A male subject approximately 40 years of age — 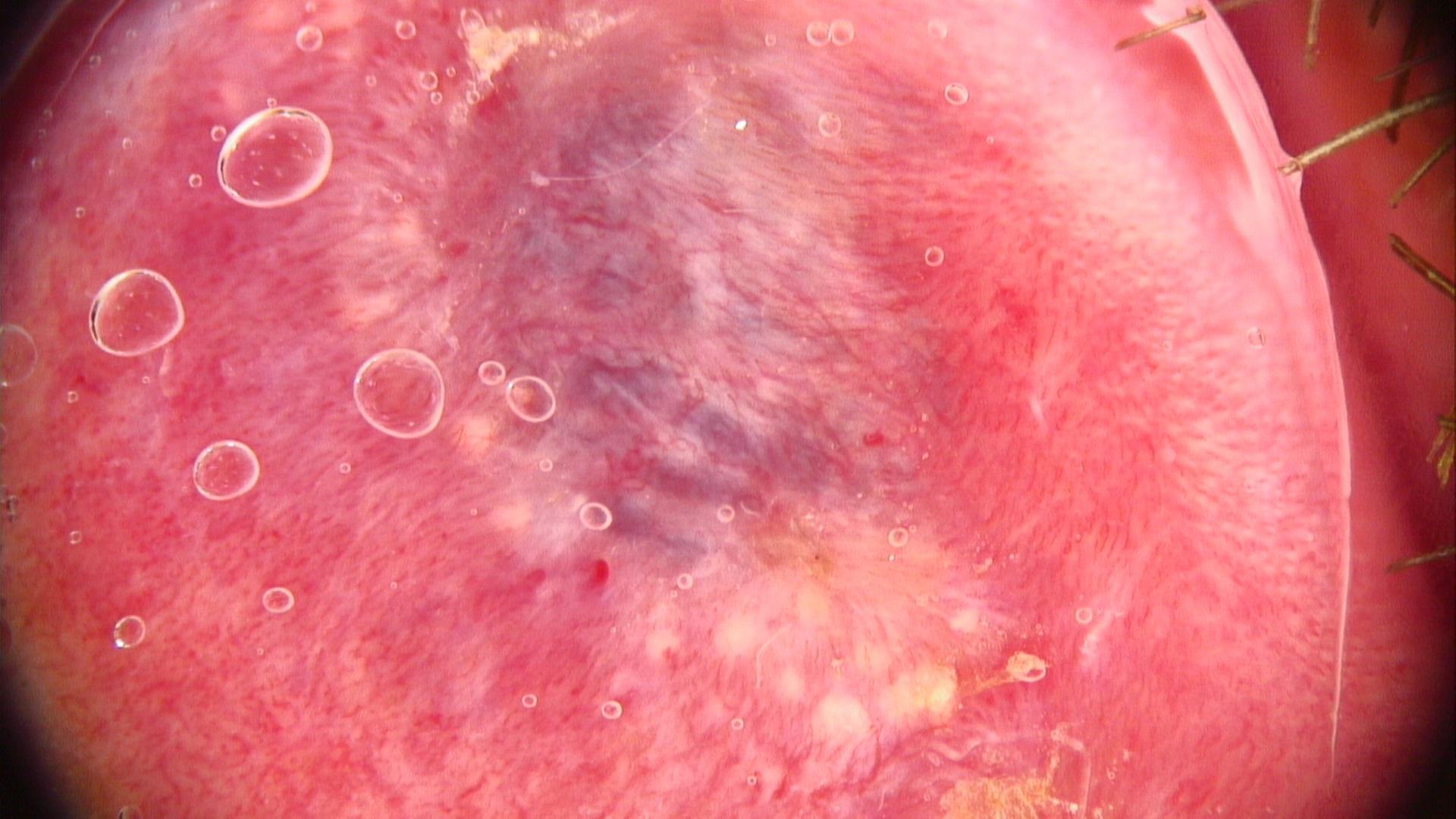Impression: Expert review favored a vascular lesion.